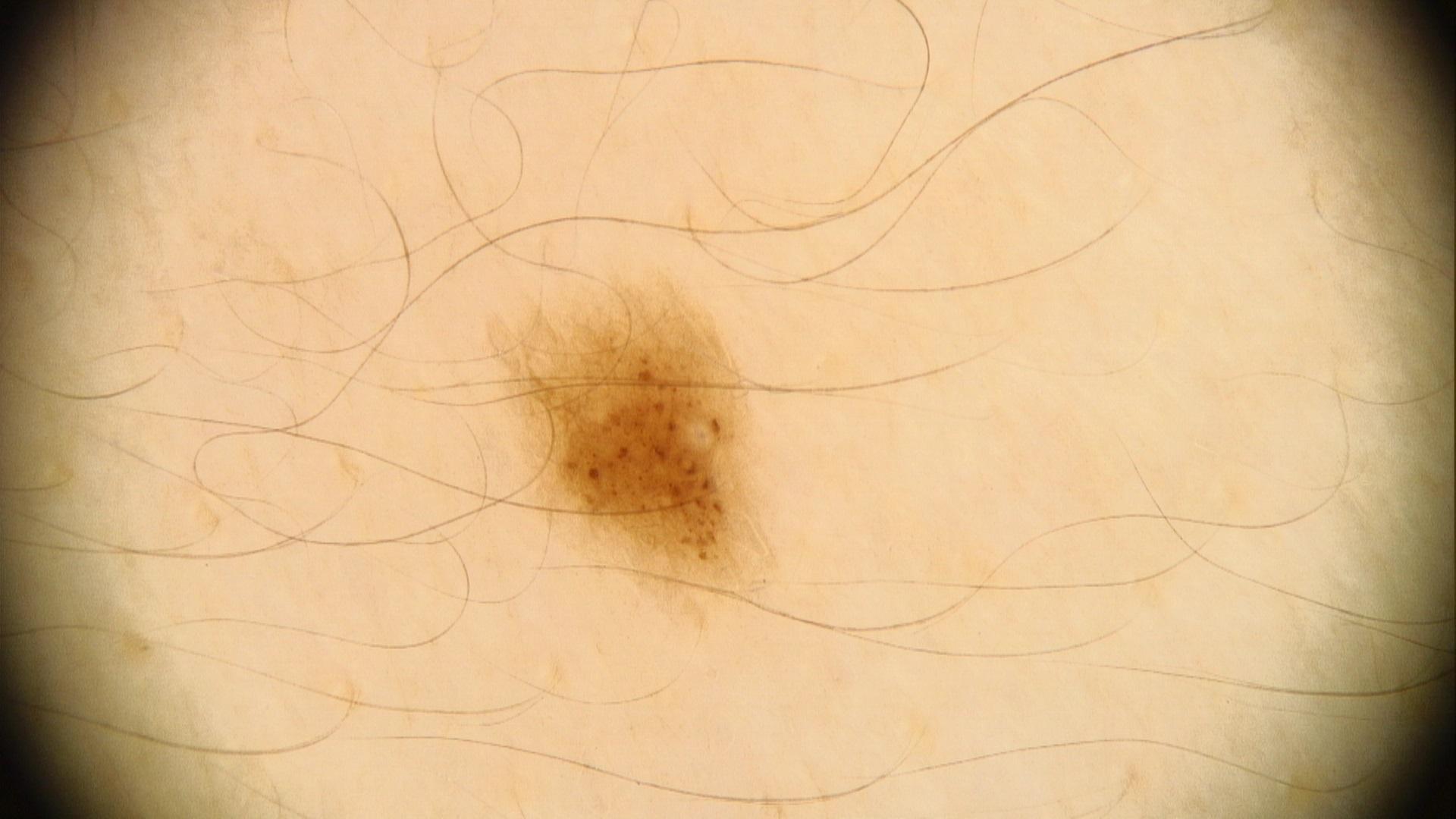Expert review favored a nevus.